Female subject, age 40–49 · the leg is involved · a close-up photograph — 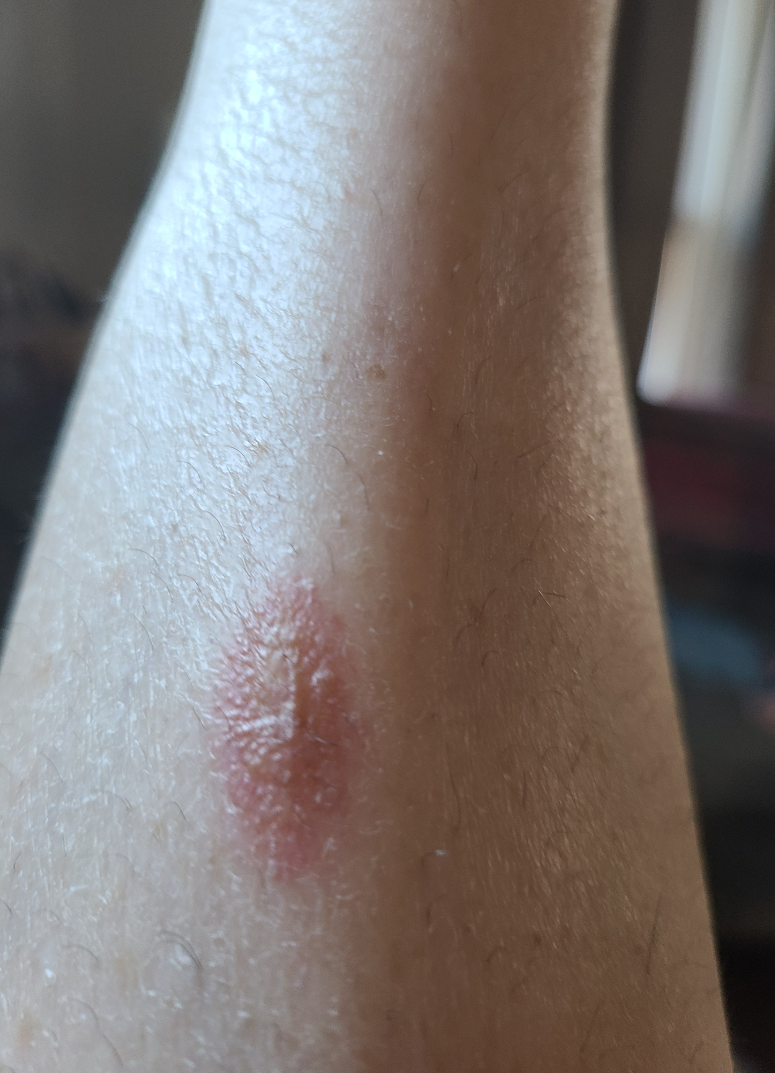| key | value |
|---|---|
| assessment | indeterminate from the photograph |